A dermatoscopic image of a skin lesion.
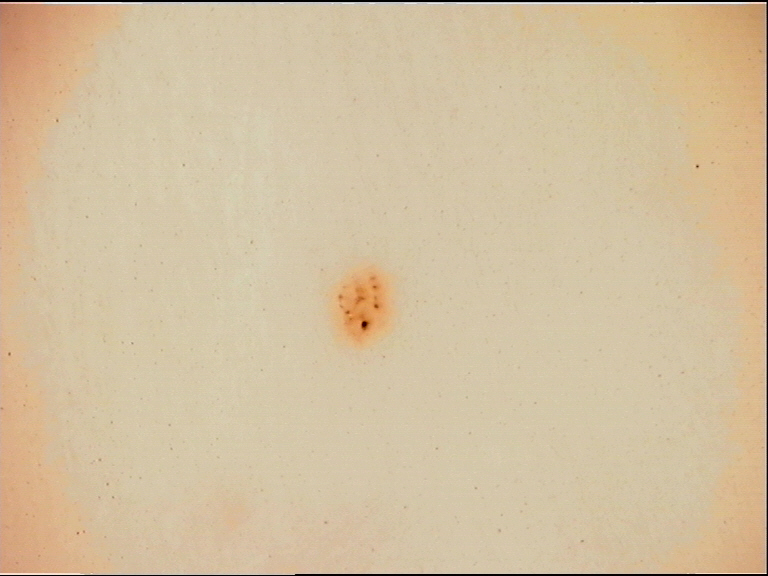The diagnosis was a banal lesion — an acral junctional nevus.